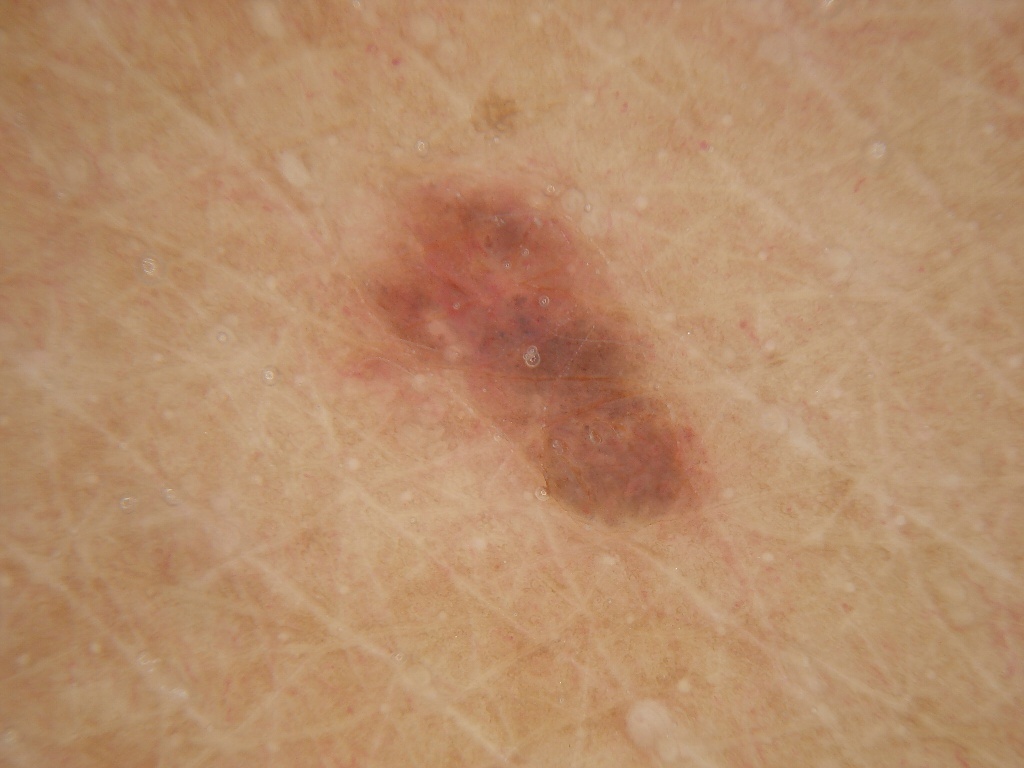Findings:
- modality: dermoscopy of a skin lesion
- lesion bbox: 304, 150, 733, 532
- lesion extent: ~13% of the field
- dermoscopic features assessed but absent: globules, pigment network, negative network, milia-like cysts, and streaks
- impression: a melanocytic nevus, a benign lesion